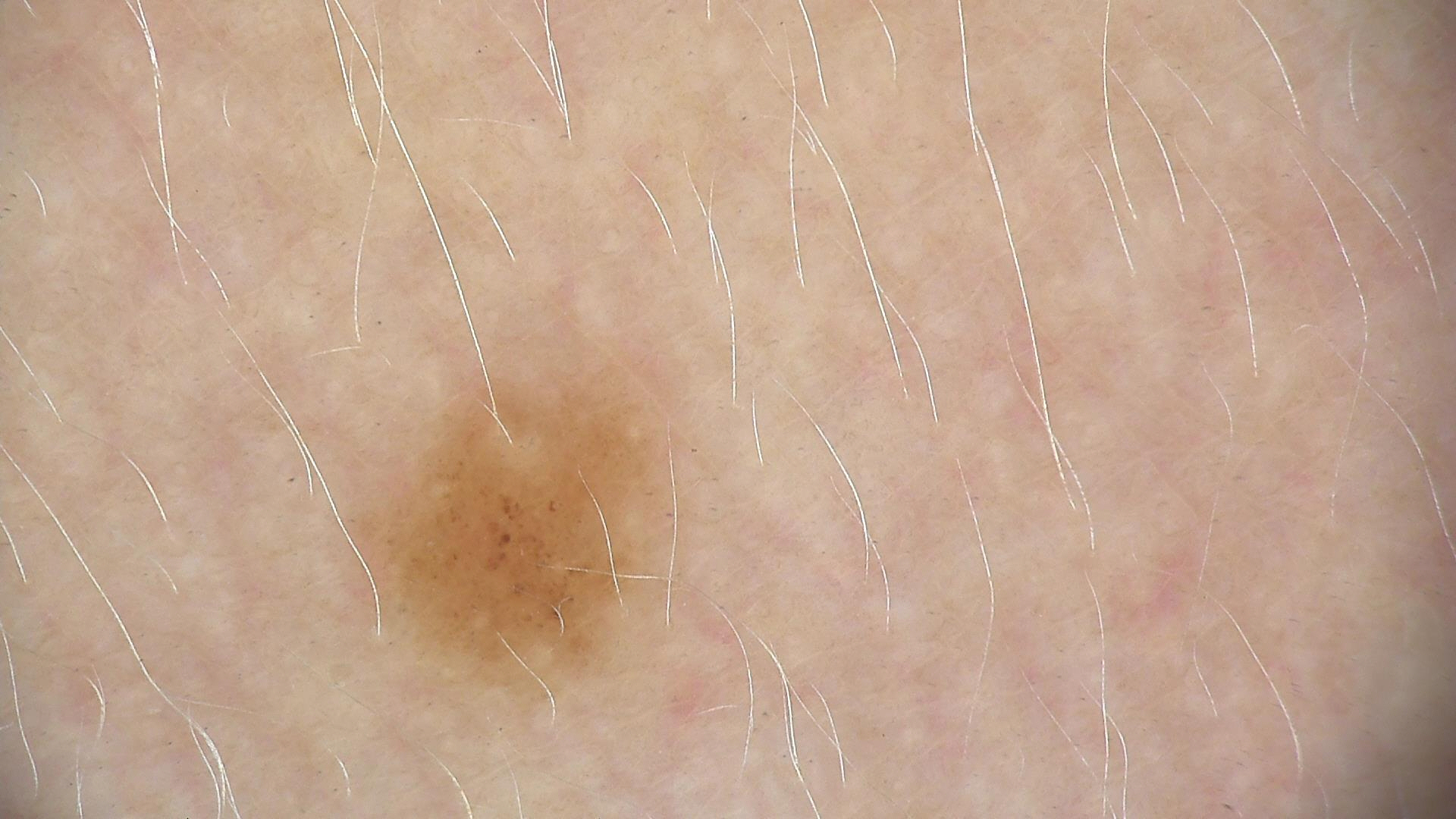Findings:
- diagnostic label: dysplastic junctional nevus (expert consensus)